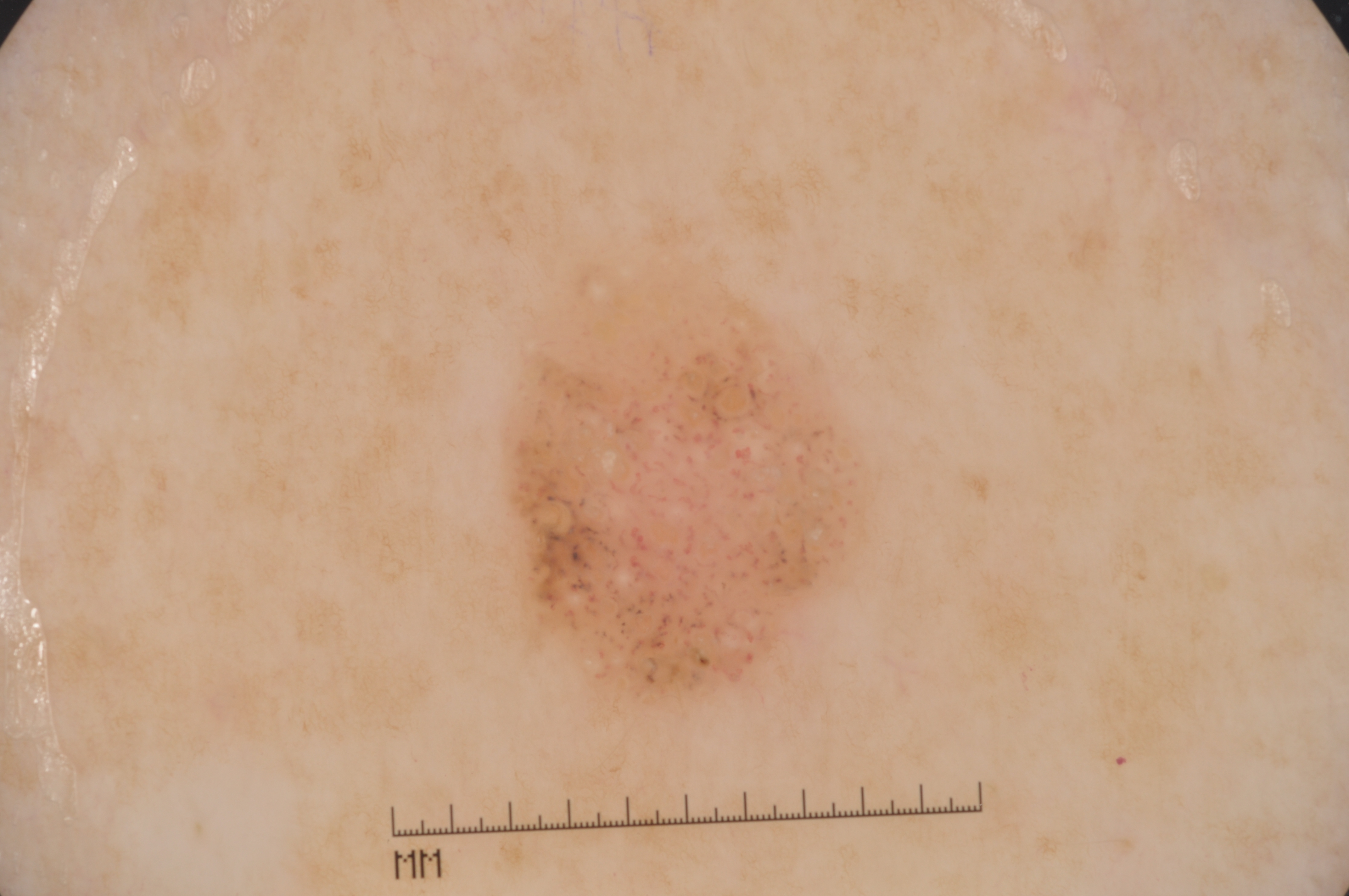Findings:
– modality · dermoscopic image
– location · 506 273 864 707
– diagnostic label · a seborrheic keratosis, a benign skin lesion